A dermatoscopic image of a skin lesion.
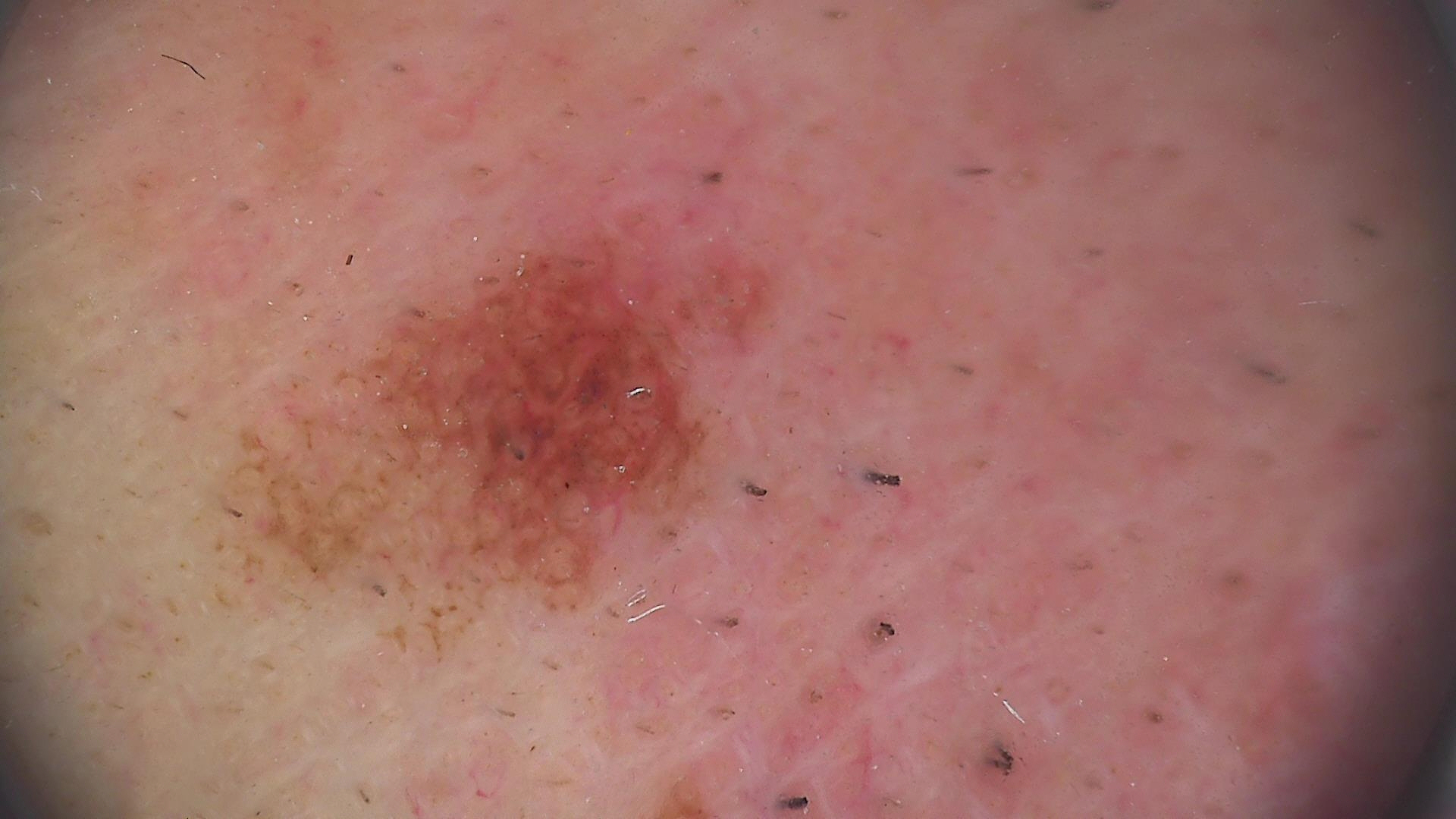category — banal
assessment — compound nevus (expert consensus)